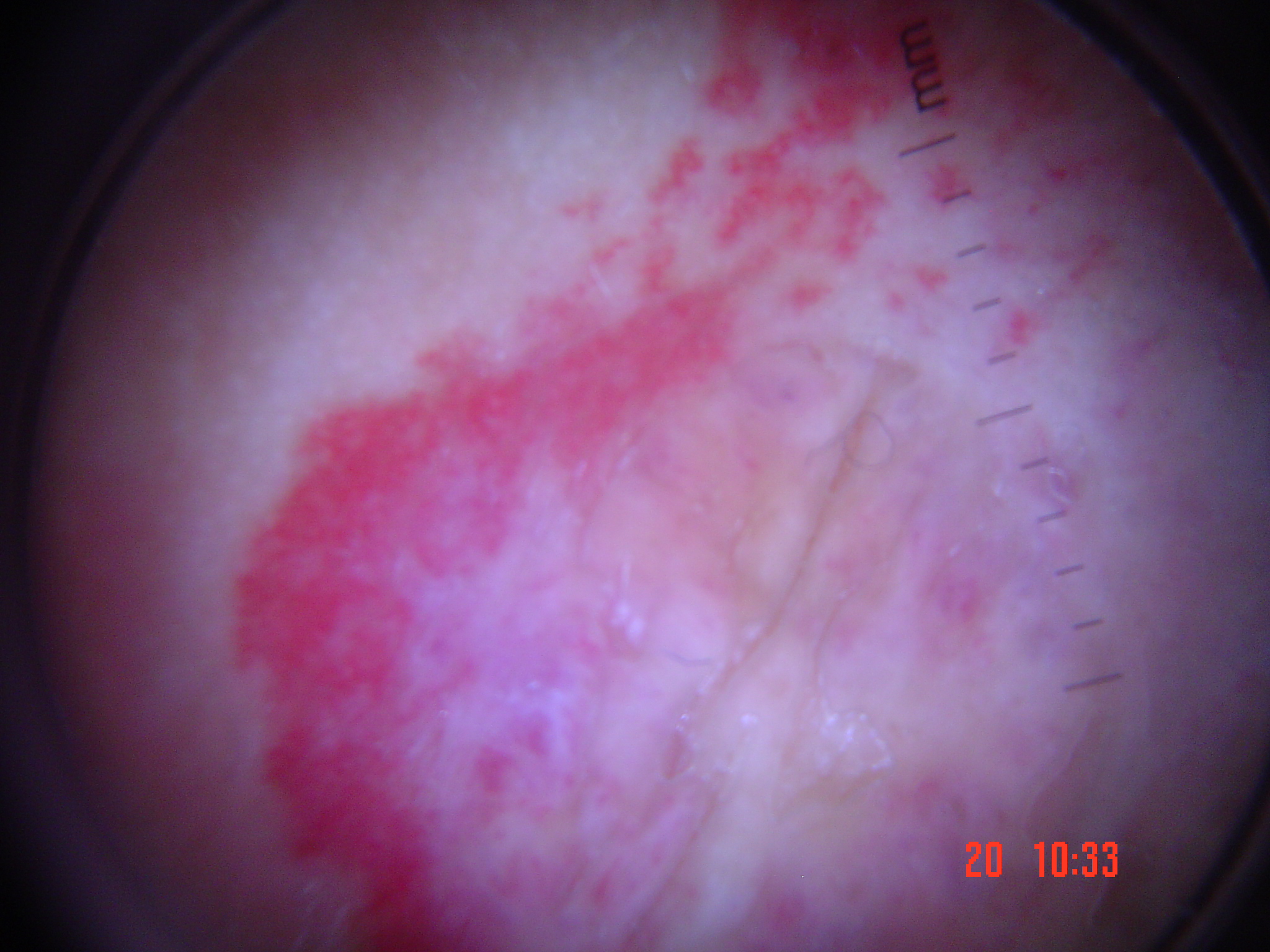Q: What kind of image is this?
A: dermoscopy
Q: What is this lesion?
A: hemangioma (expert consensus)